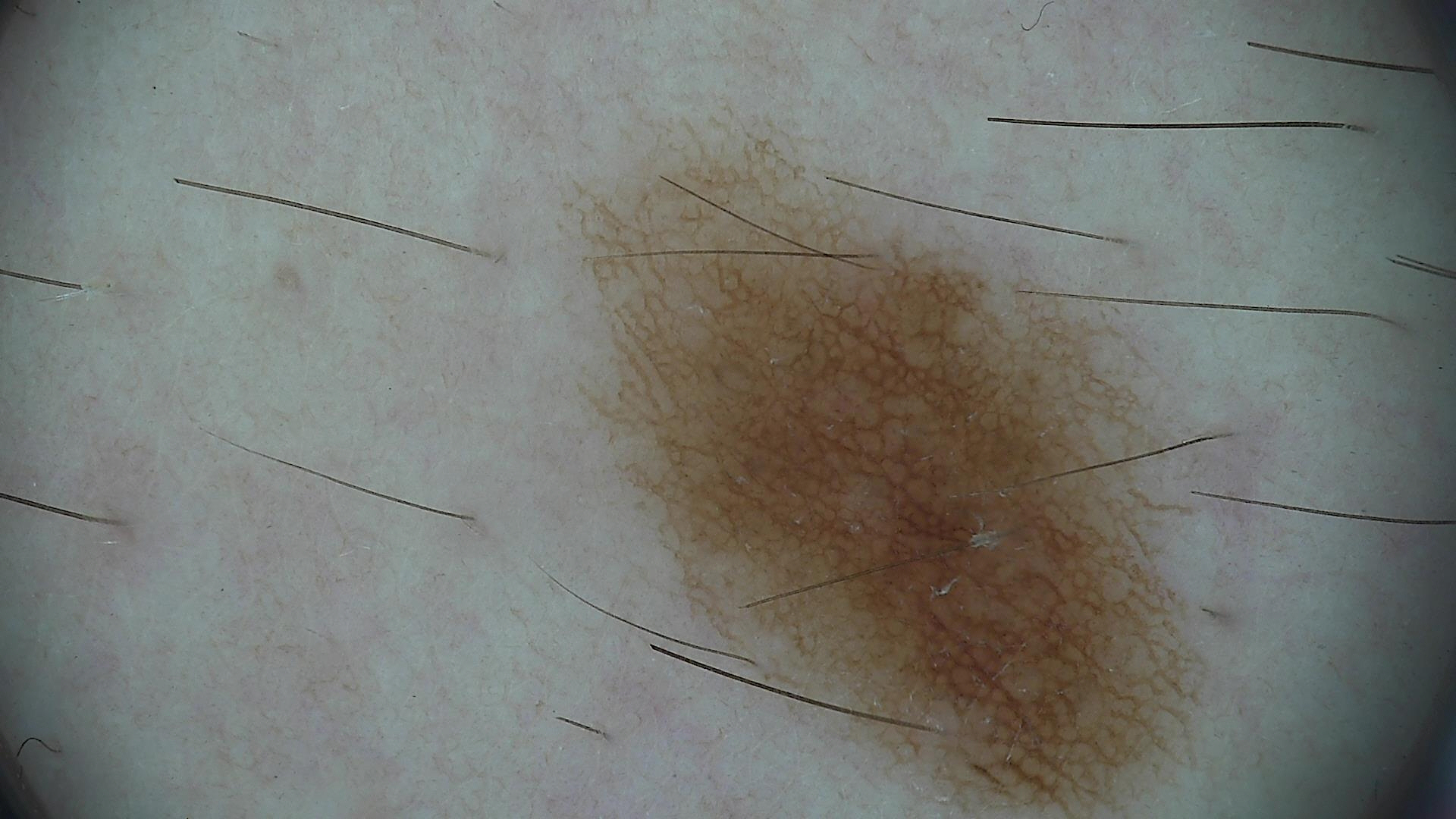Q: What kind of image is this?
A: dermatoscopy
Q: What was the diagnostic impression?
A: dysplastic junctional nevus (expert consensus)